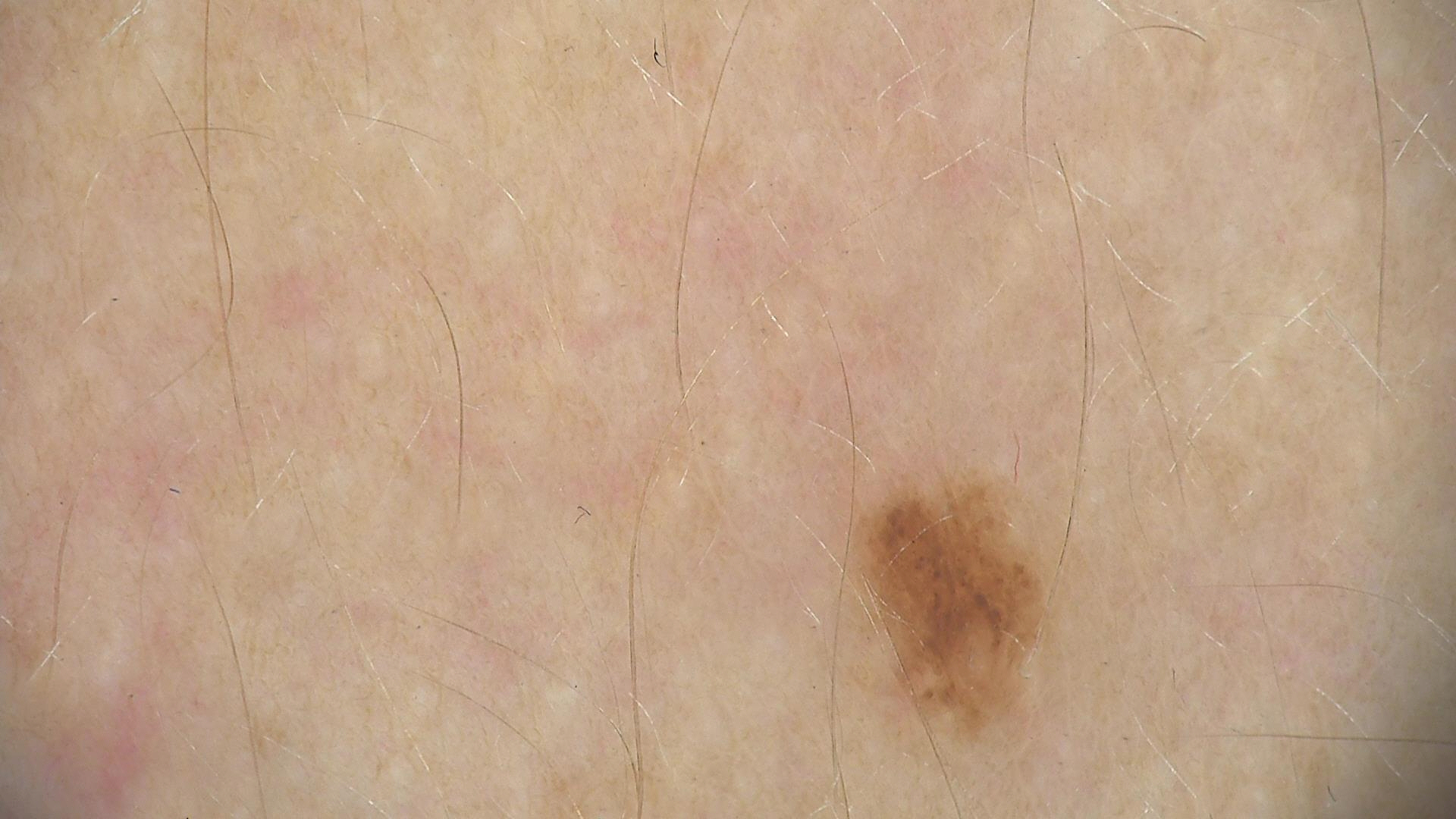Labeled as a benign lesion — a dysplastic junctional nevus.